The photograph is a close-up of the affected area: 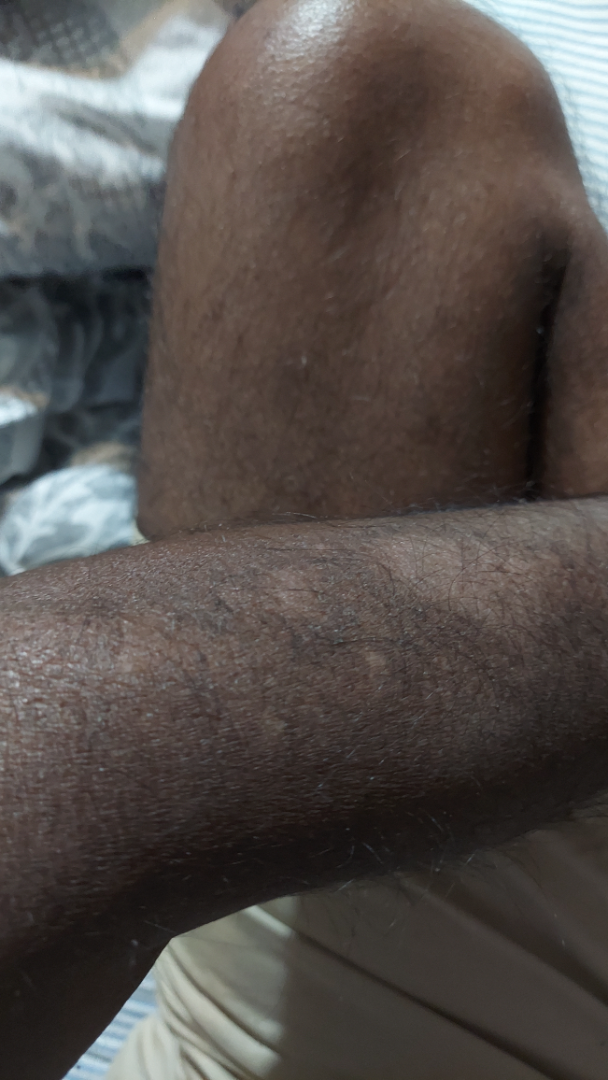| key | value |
|---|---|
| assessment | indeterminate from the photograph |